The patient reported no systemic symptoms. The patient described the issue as a rash. The photo was captured at an angle. The lesion is described as raised or bumpy. Reported lesion symptoms include itching. The subject is female. The top or side of the foot and leg are involved.
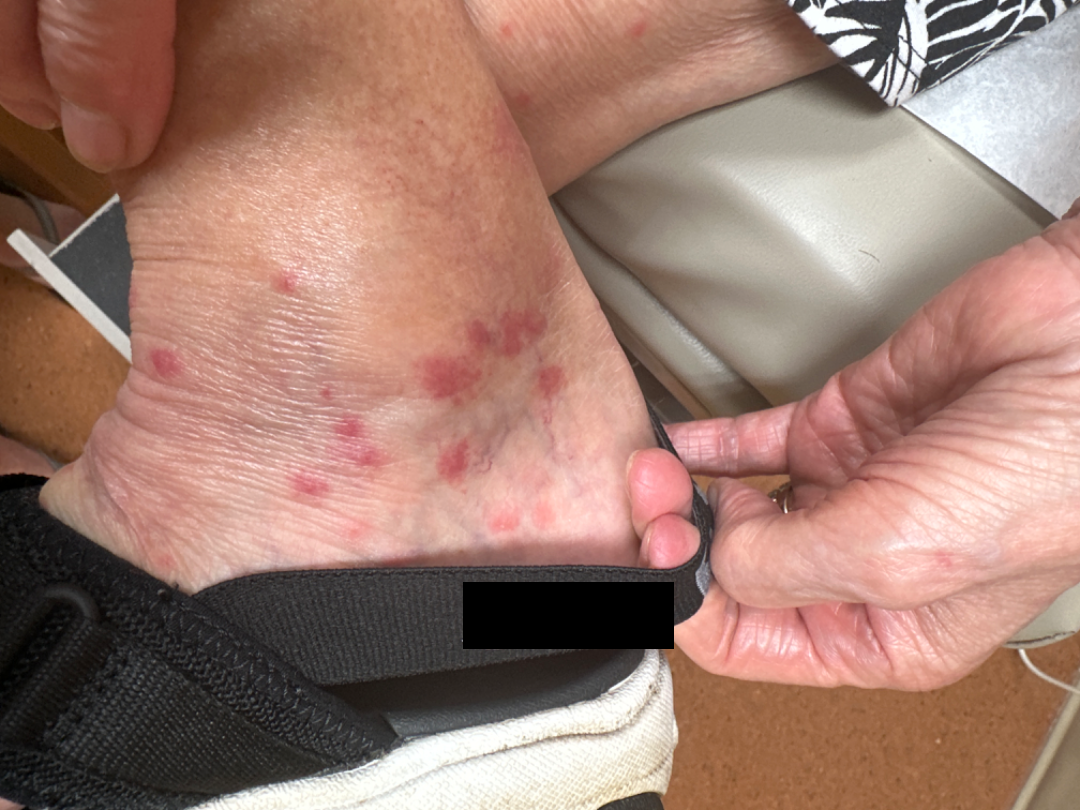Reviewed remotely by one dermatologist: the impression was split between Insect Bite and Leukocytoclastic Vasculitis.